No relevant systemic symptoms. This image was taken at an angle. Reported lesion symptoms include itching. The contributor reports the lesion is raised or bumpy. The arm is involved: 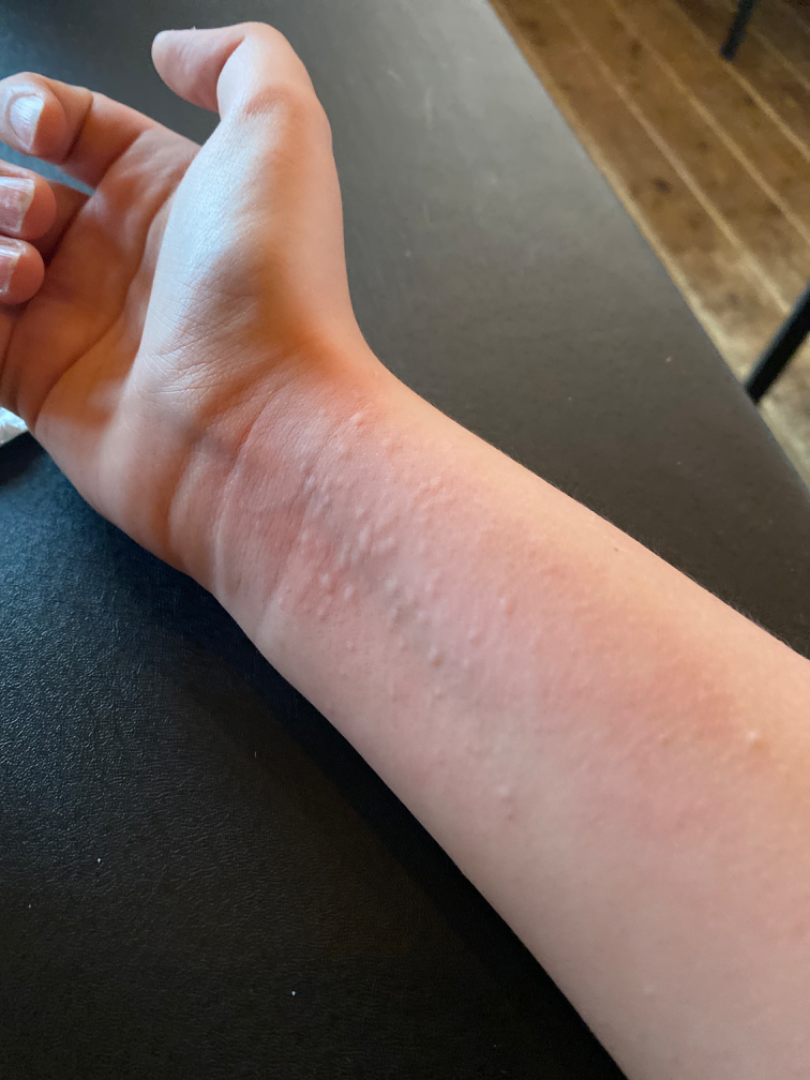clinical impression = consistent with Urticaria.